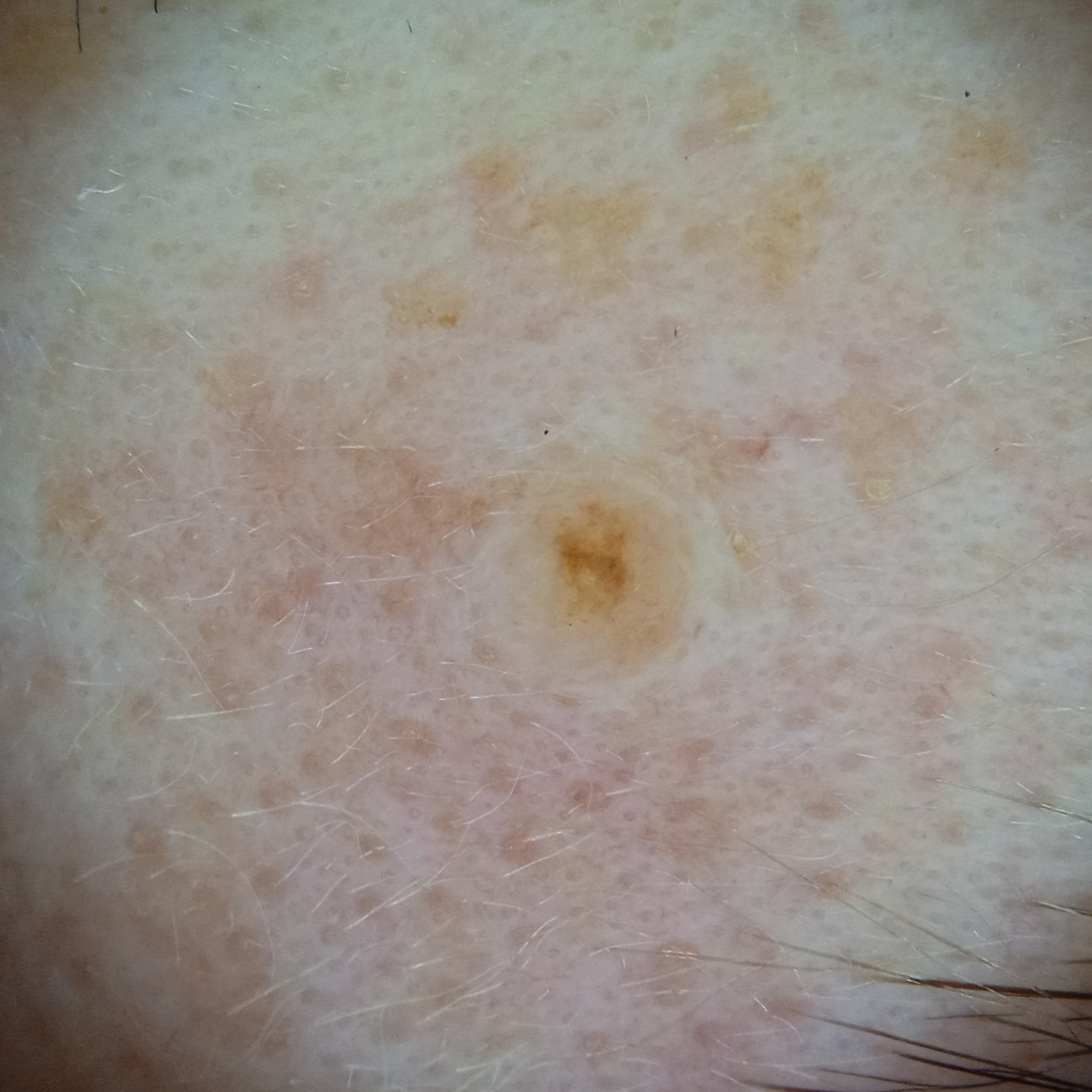Clinical context: A dermatoscopic image of a skin lesion. The patient says their skin reddens painfully with sun exposure. The patient describes having a moderate number of moles. The referring clinician suspected melanoma. On a questionnaire the patient reported no family history of skin cancer. A female patient 50 years old. The lesion involves the face. Impression: The lesion was assessed as a melanocytic nevus.